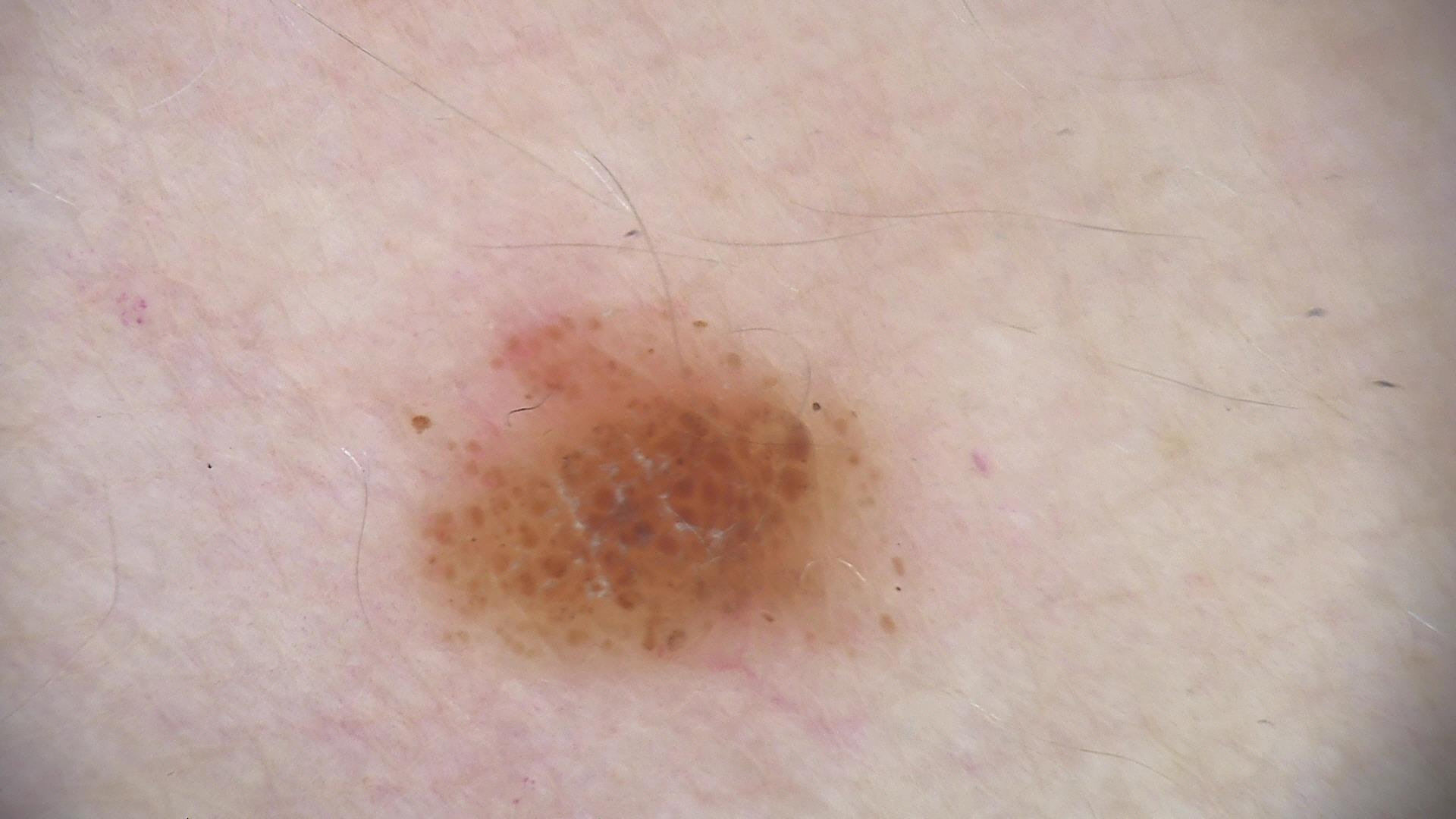Summary: Dermoscopy of a skin lesion. Conclusion: Labeled as a banal lesion — a compound nevus.